The subject is 18–29, male · symptoms reported: enlargement and bothersome appearance · the patient described the issue as a rash · the lesion involves the arm · texture is reported as raised or bumpy · close-up view · the patient indicates the condition has been present for one to three months:
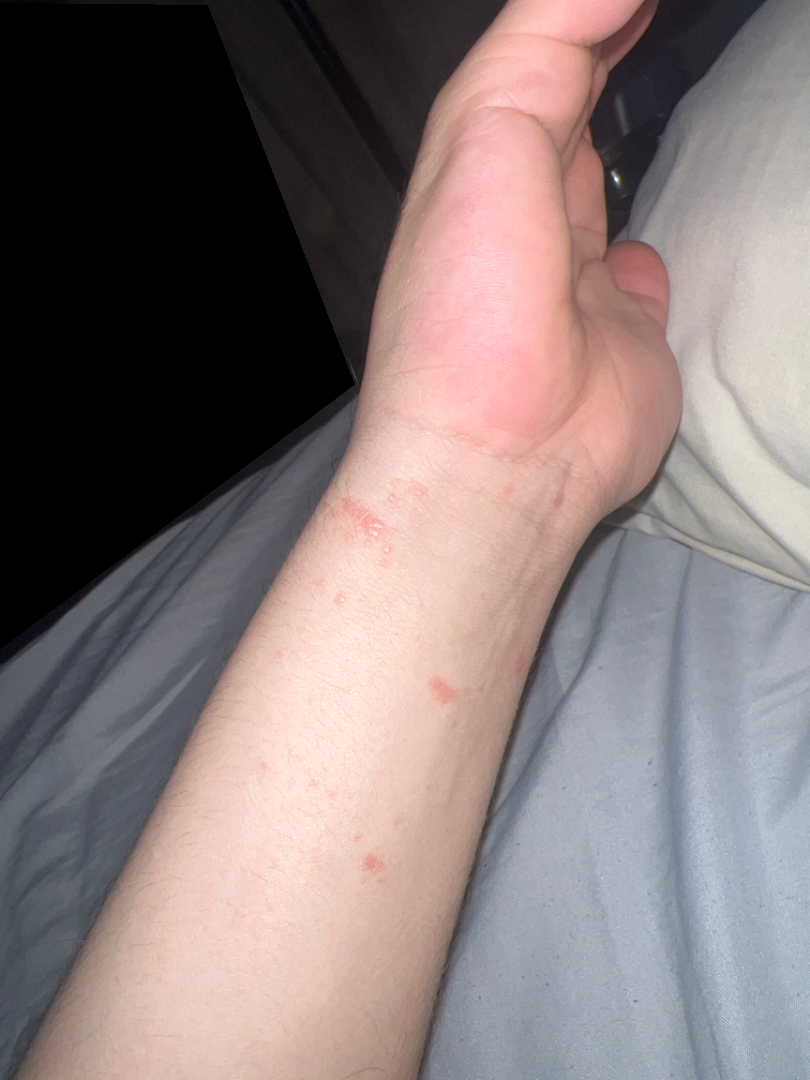Q: What conditions are considered?
A: favoring Allergic Contact Dermatitis; an alternative is Lichen nitidus; less probable is Verruca vulgaris; lower on the differential is Molluscum Contagiosum